Located on the leg and arm · the photograph is a close-up of the affected area — 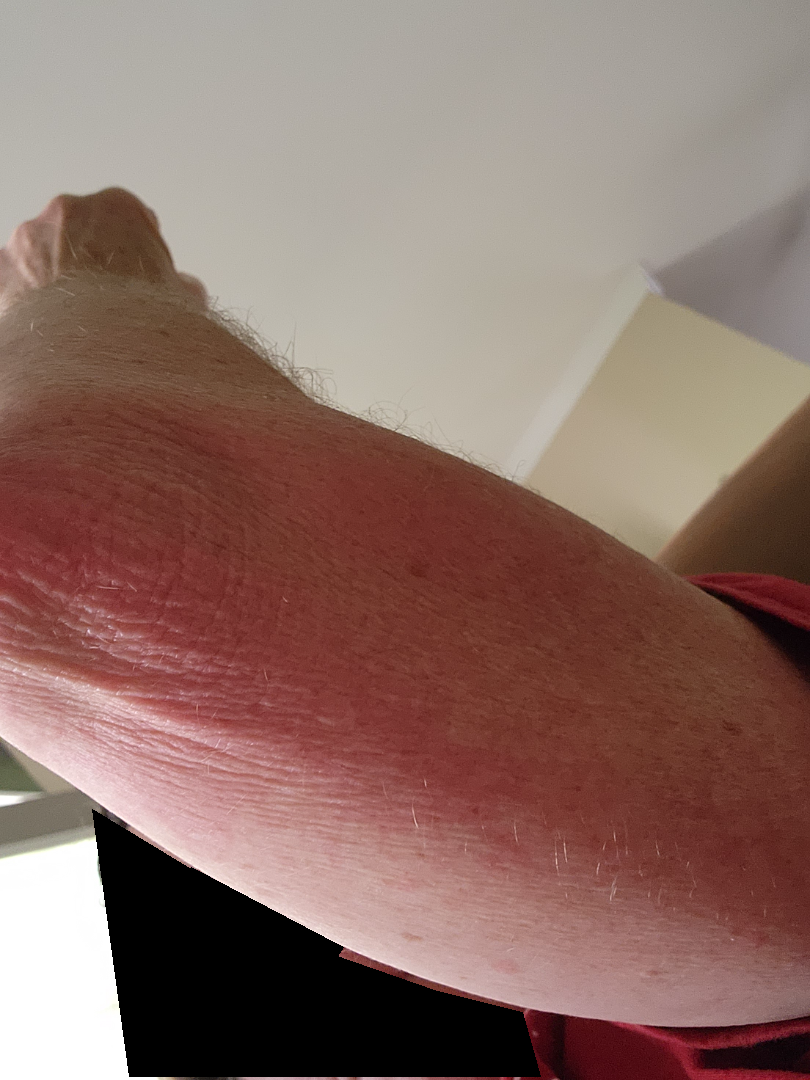assessment: could not be assessed | constitutional symptoms: none reported | onset: about one day | lesion texture: raised or bumpy | reported symptoms: burning | self-categorized as: a rash.